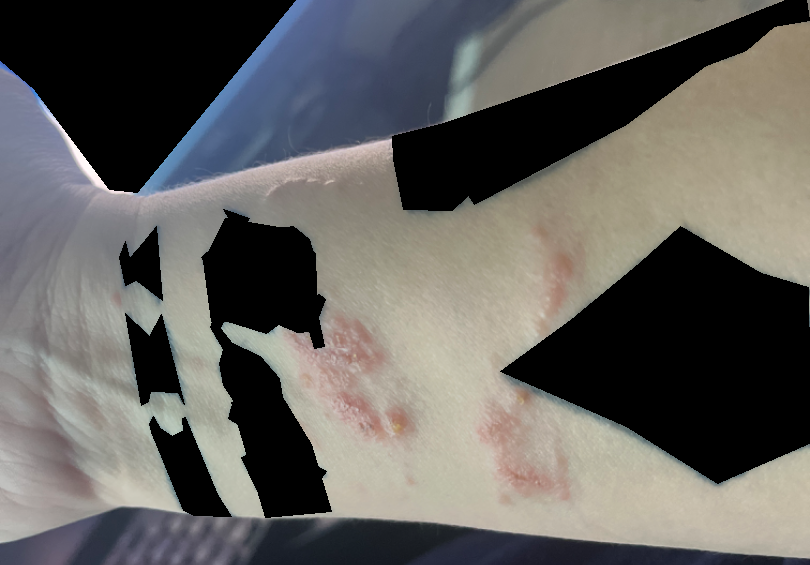Diagnostic features were not clearly distinguishable in this photograph. The arm is involved. This is a close-up image.